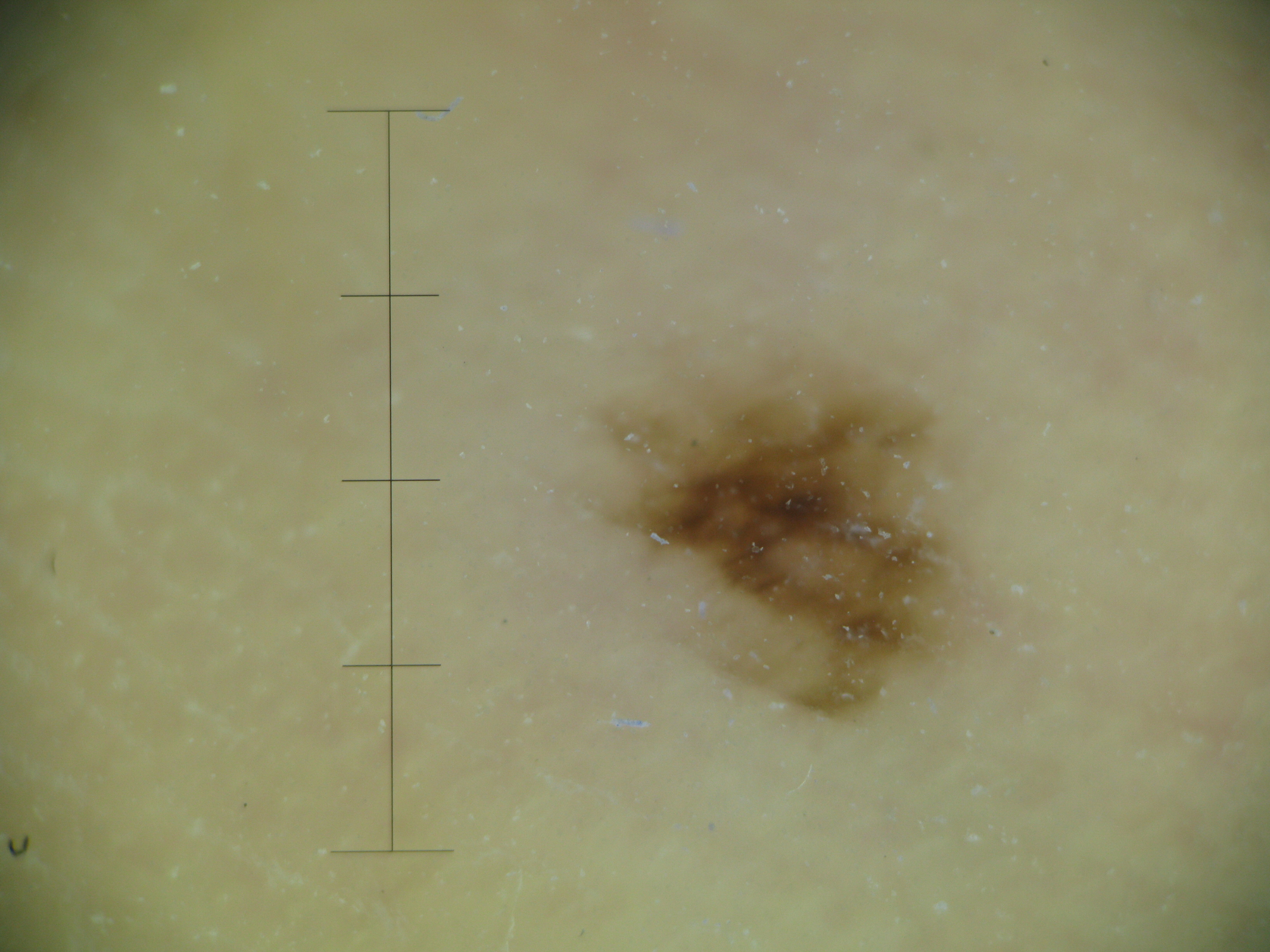image: dermatoscopy; class: acral dysplastic junctional nevus (expert consensus).